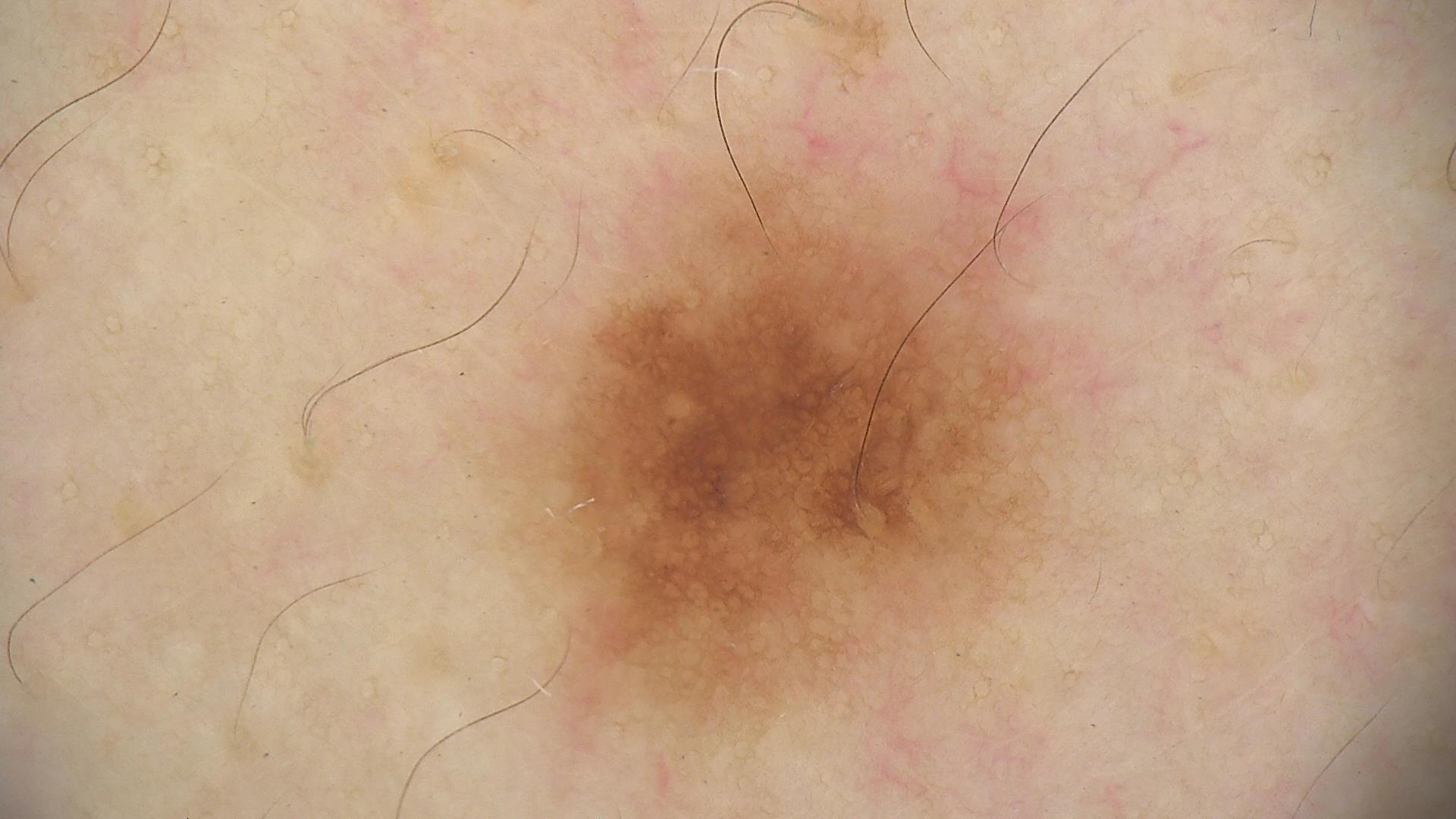Q: What is this lesion?
A: dysplastic junctional nevus (expert consensus)